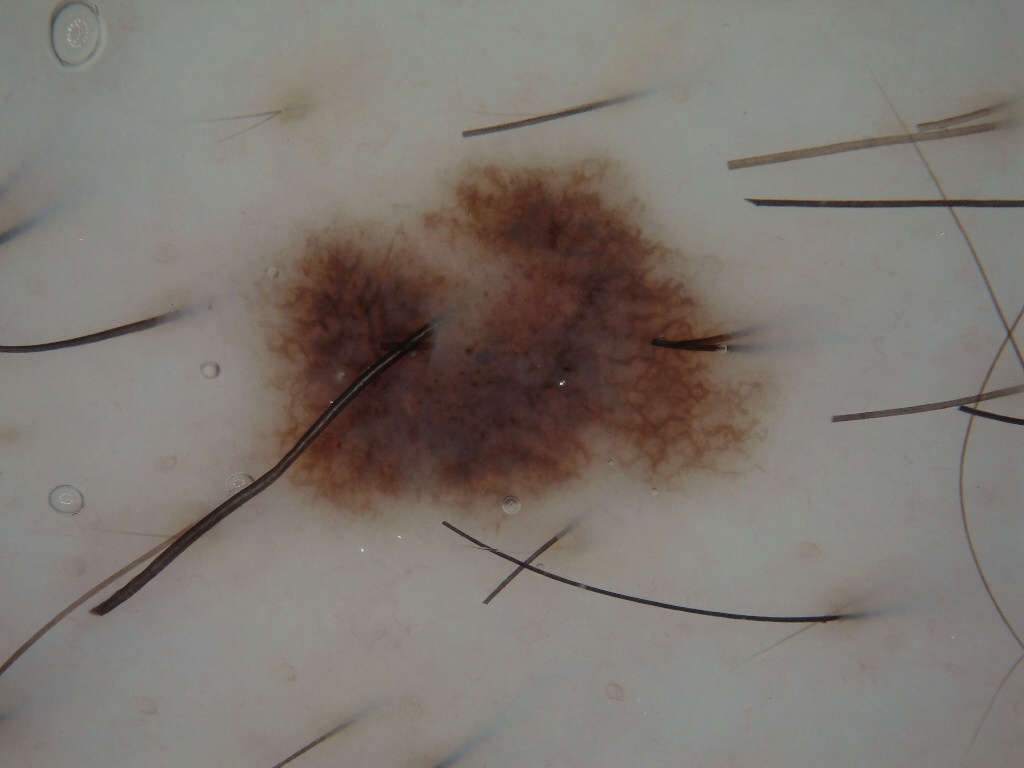This is a dermoscopic photograph of a skin lesion. The lesion occupies the region [227,140,784,538]. Dermoscopic review identifies streaks and globules. The lesion takes up about 23% of the image. Diagnosed as a benign lesion.